A dermoscopy image of a single skin lesion: 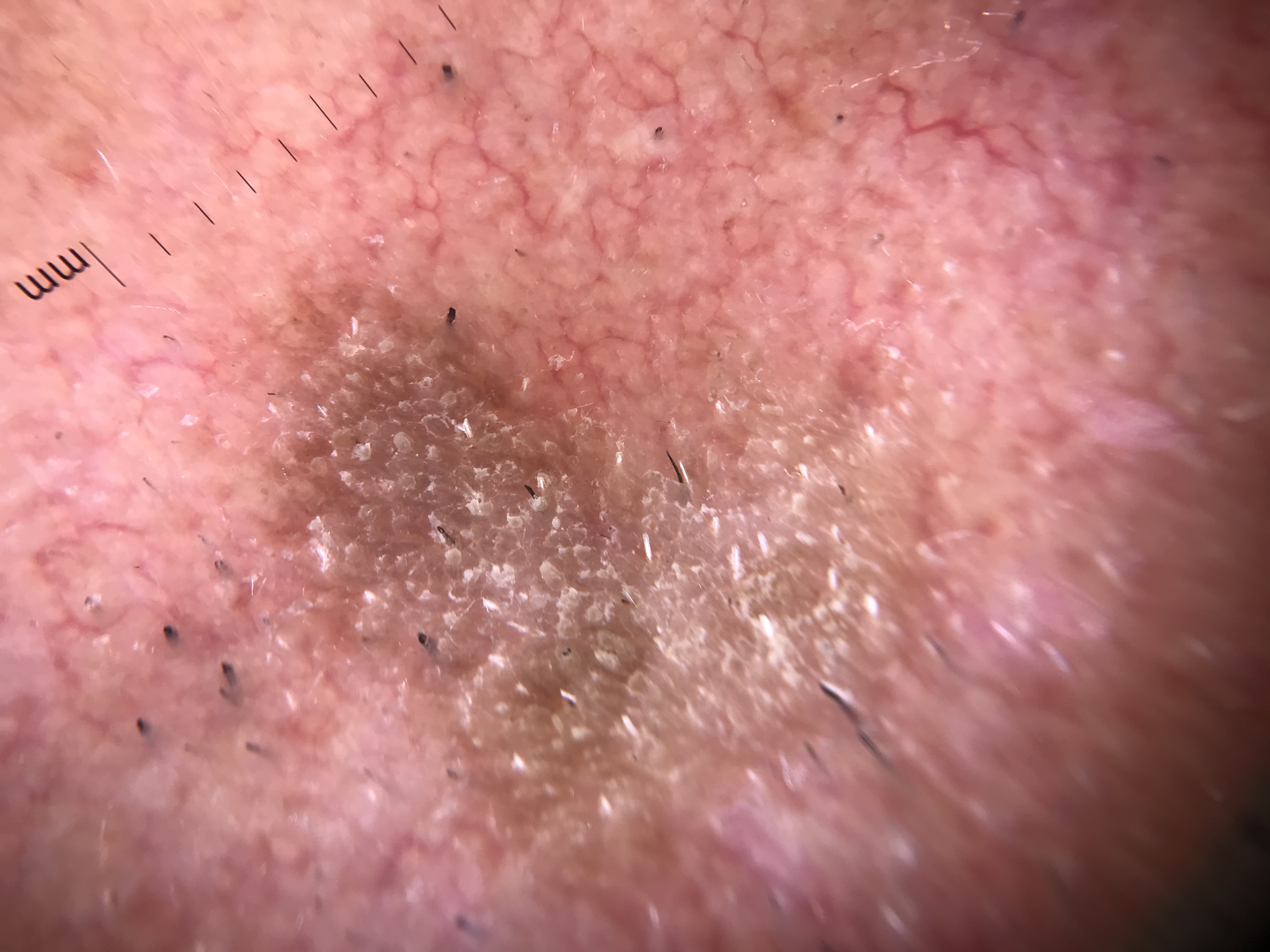The architecture is that of a keratinocytic lesion. The diagnostic label was a benign lesion — a seborrheic keratosis.